Dermoscopy of a skin lesion. The patient says their skin reddens with sun exposure. The patient describes having a moderate number of moles. A female subject 27 years old — 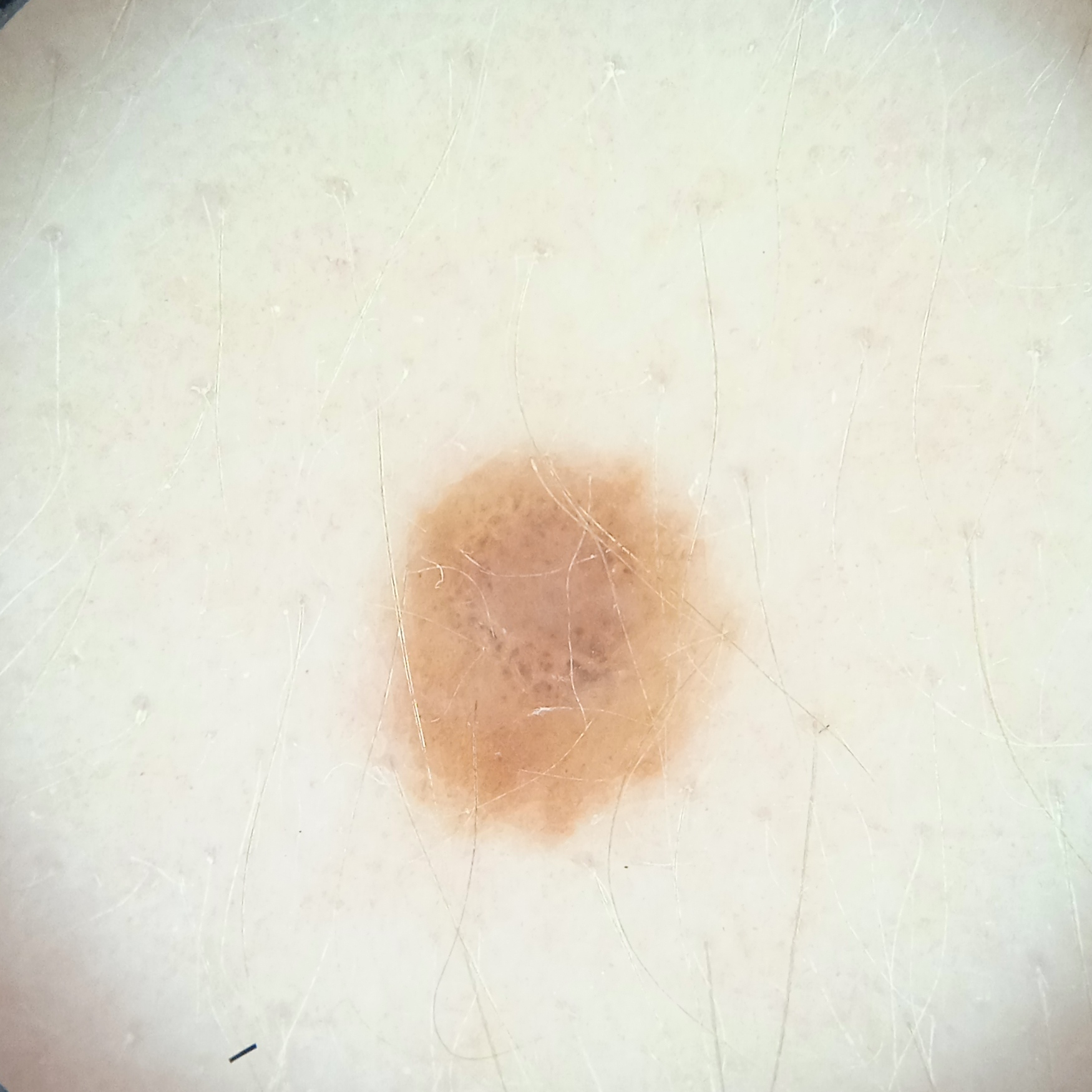Q: Where is the lesion?
A: the torso
Q: Lesion size?
A: 4.4 mm
Q: What was the diagnosis?
A: melanocytic nevus (dermatologist consensus)